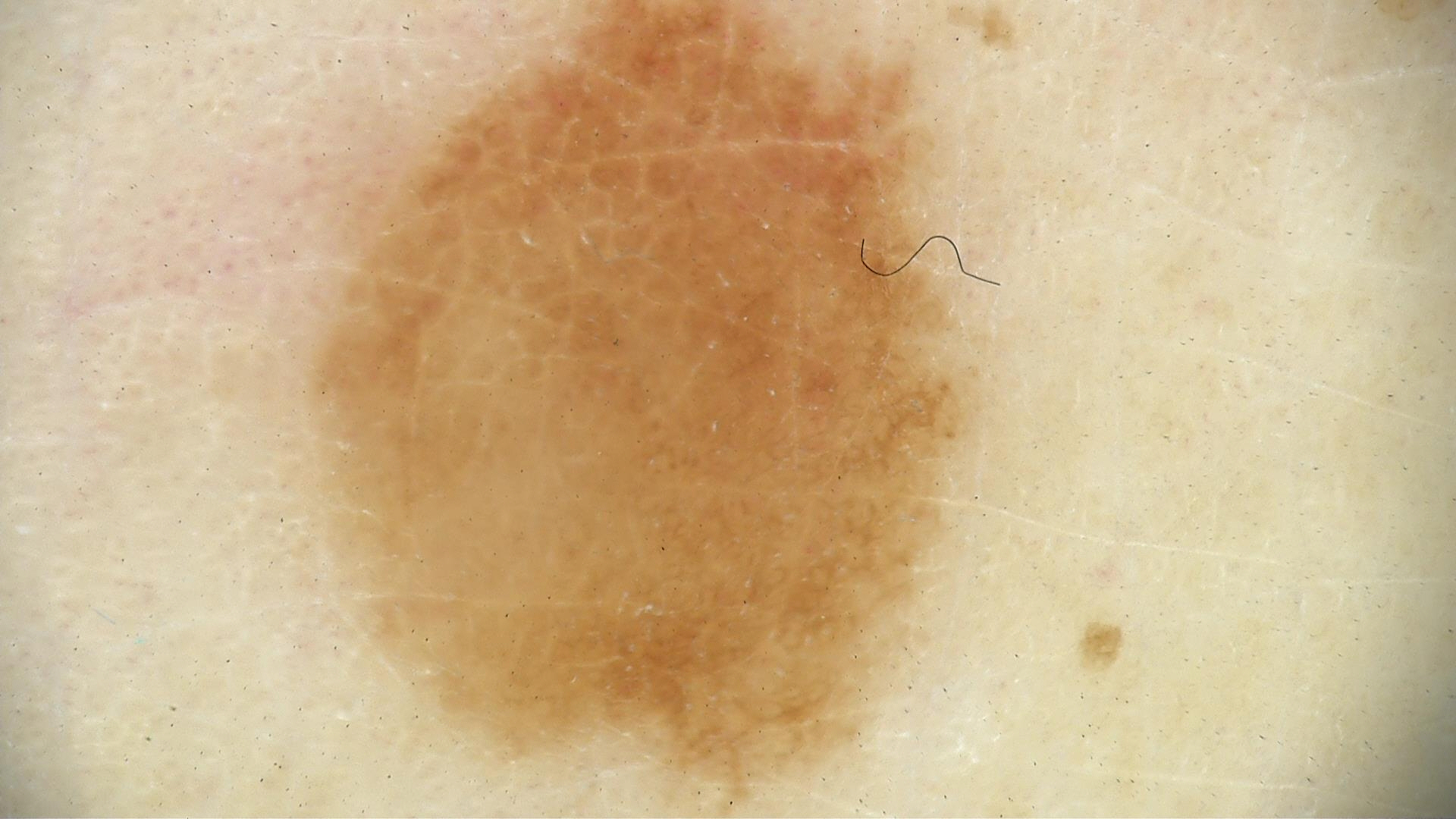Dermoscopy of a skin lesion.
The diagnosis was a banal lesion — a junctional nevus.